Texture is reported as raised or bumpy. The affected area is the arm, leg and front of the torso. Present for about one day. The photograph is a close-up of the affected area. No relevant systemic symptoms. The contributor is a male aged 18–29 — 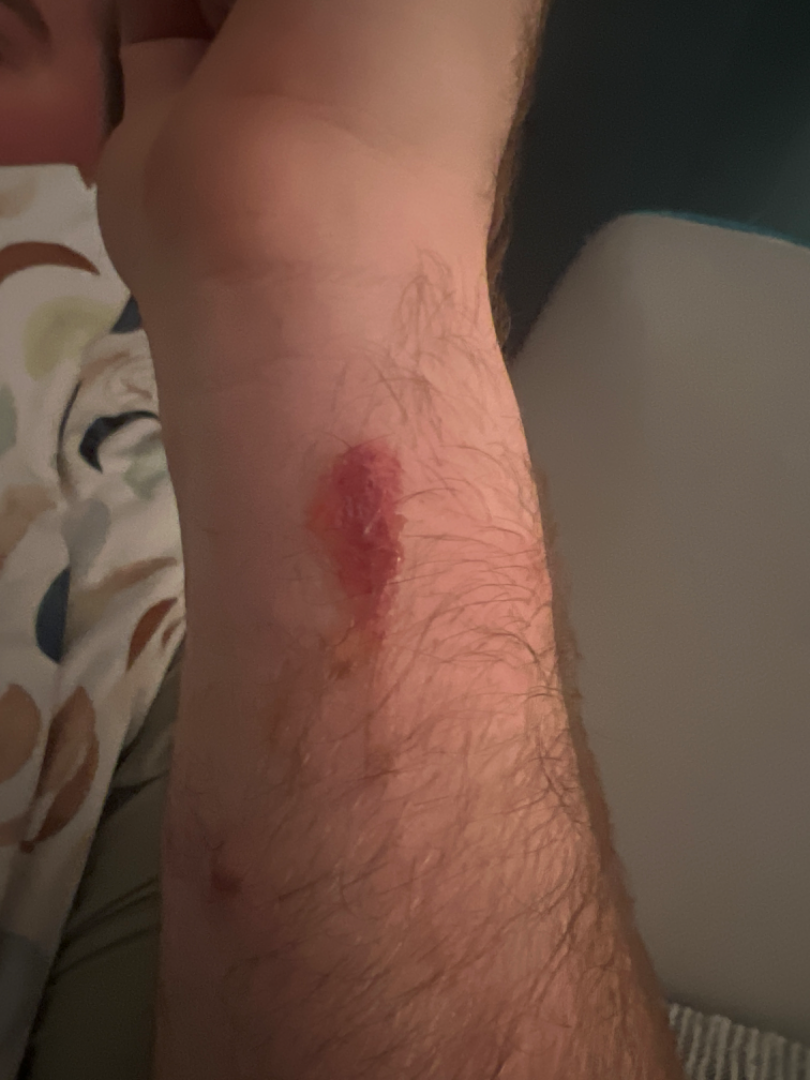Review: The reviewing clinician's impression was: the differential, in no particular order, includes Burn of skin and Abrasion, scrape, or scab.